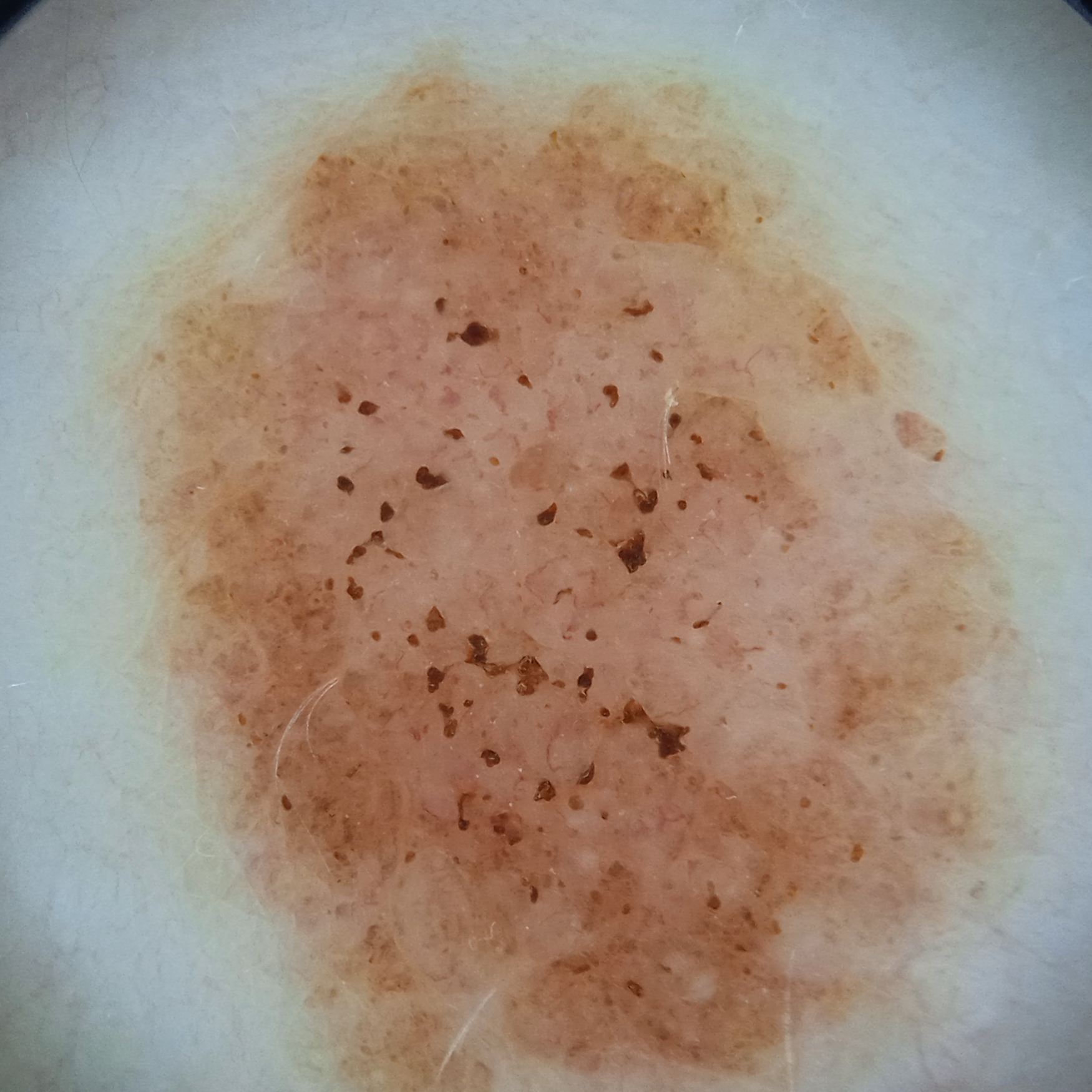Q: What was the diagnosis?
A: melanocytic nevus (dermatologist consensus)